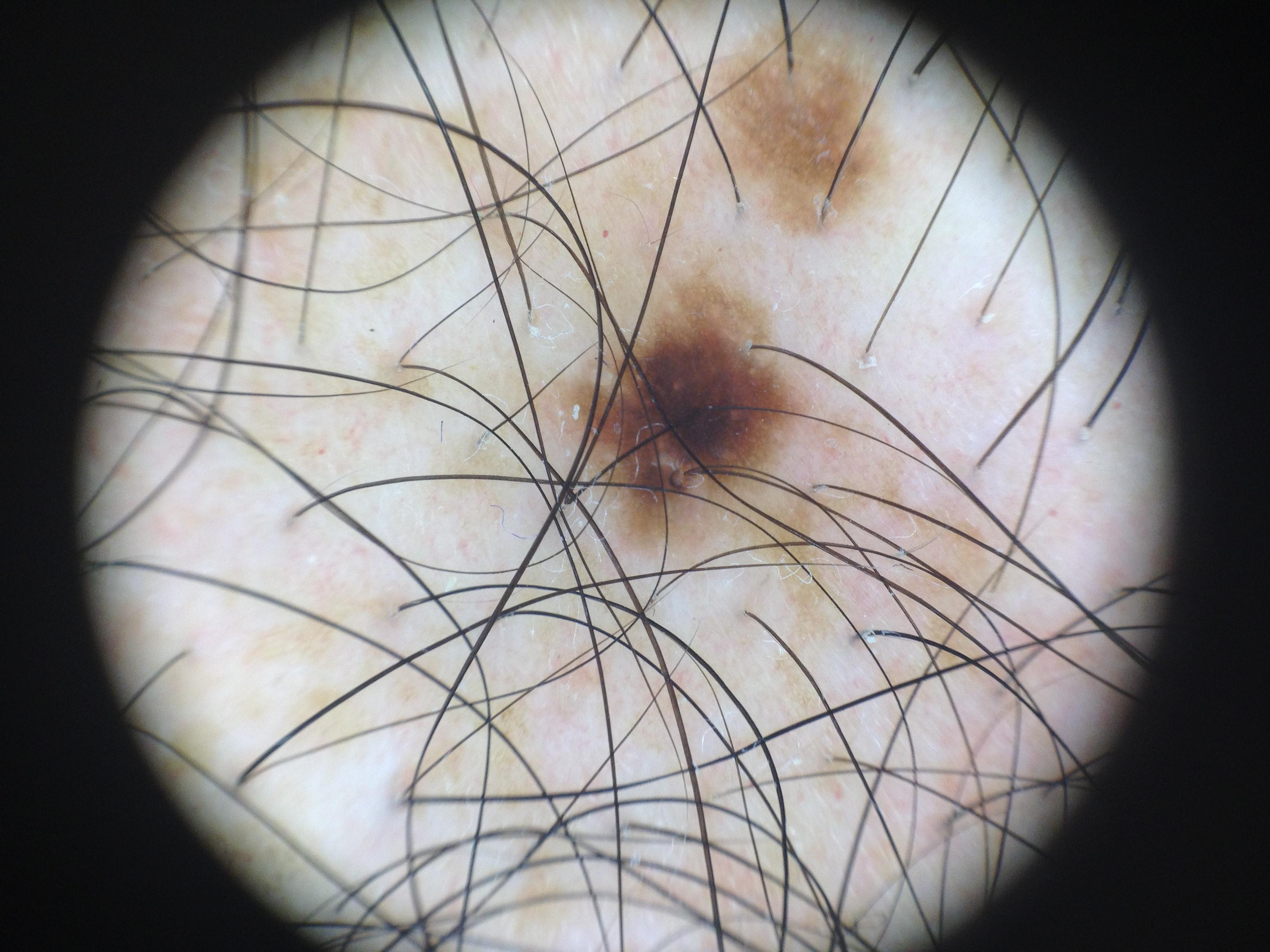Case summary:
The chart notes a prior melanoma but no first-degree relative with melanoma. A male subject in their mid- to late 50s. The patient is Fitzpatrick phototype II. A dermatoscopic image of a skin lesion. The lesion was found on the trunk.
Conclusion:
Expert review favored a benign lesion — a nevus.